The affected area is the leg, arm and back of the torso. An image taken at a distance: 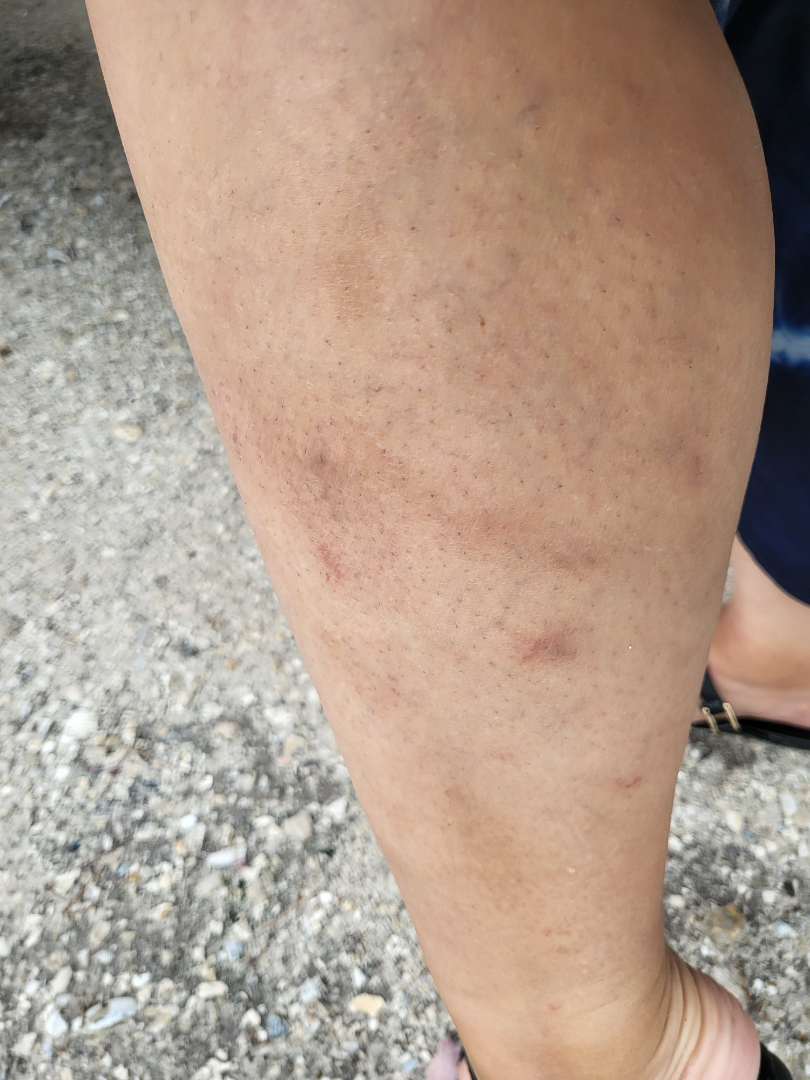Impression:
The reviewing dermatologist was unable to assign a differential diagnosis from the image.
History:
Present for one to four weeks. The patient described the issue as a rash. Symptoms reported: itching.